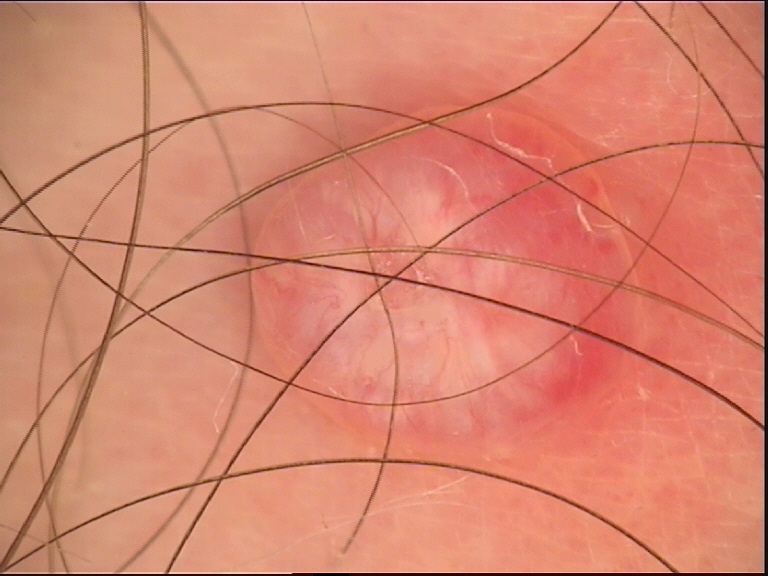Biopsy-confirmed as a basal cell carcinoma.